Reported duration is one to four weeks · the patient described the issue as a rash · this image was taken at an angle · the palm is involved · the contributor notes the lesion is raised or bumpy · the contributor notes bothersome appearance · the contributor is 18–29, female:
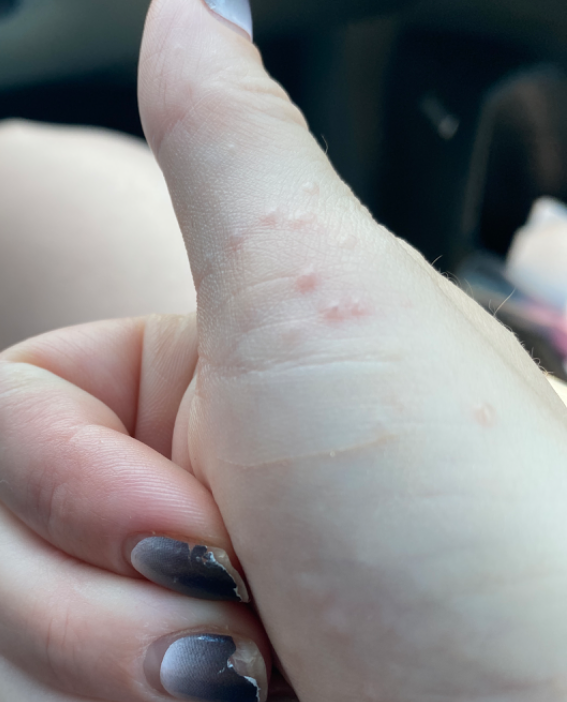Q: What conditions are considered?
A: the differential, in no particular order, includes Verruca vulgaris and Molluscum Contagiosum; a remote consideration is Acrokeratosis verruciformis